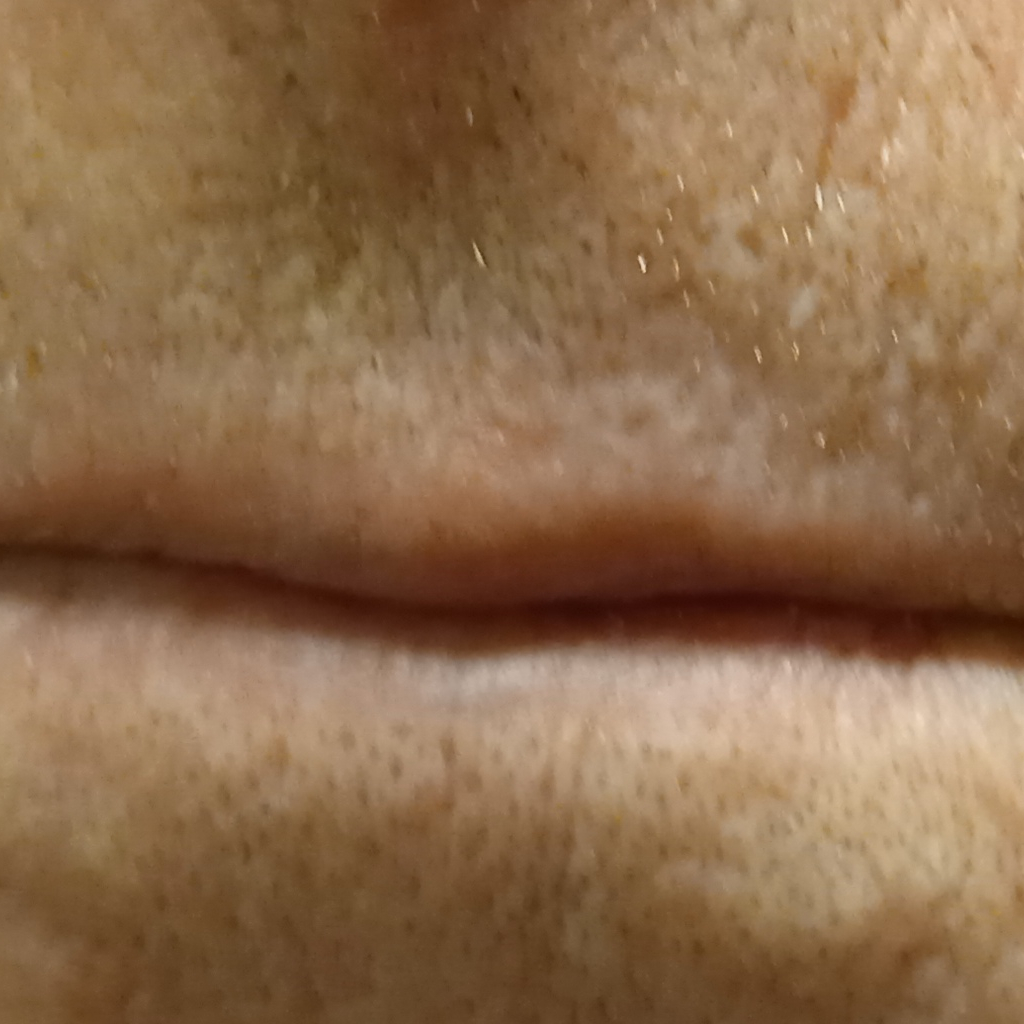| feature | finding |
|---|---|
| sun reaction | skin reddens with sun exposure |
| clinical context | research study (no referral diagnosis) |
| nevus count | a moderate number of melanocytic nevi |
| risk factors | a personal history of skin cancer, a personal history of cancer |
| subject | male, aged 77 |
| site | the face |
| size | 6.4 mm |
| diagnosis | actinic keratosis (dermatologist consensus) |